Reported lesion symptoms include bothersome appearance, enlargement and burning · the affected area is the top or side of the foot · female subject, age 18–29 · close-up view · the patient considered this a rash:
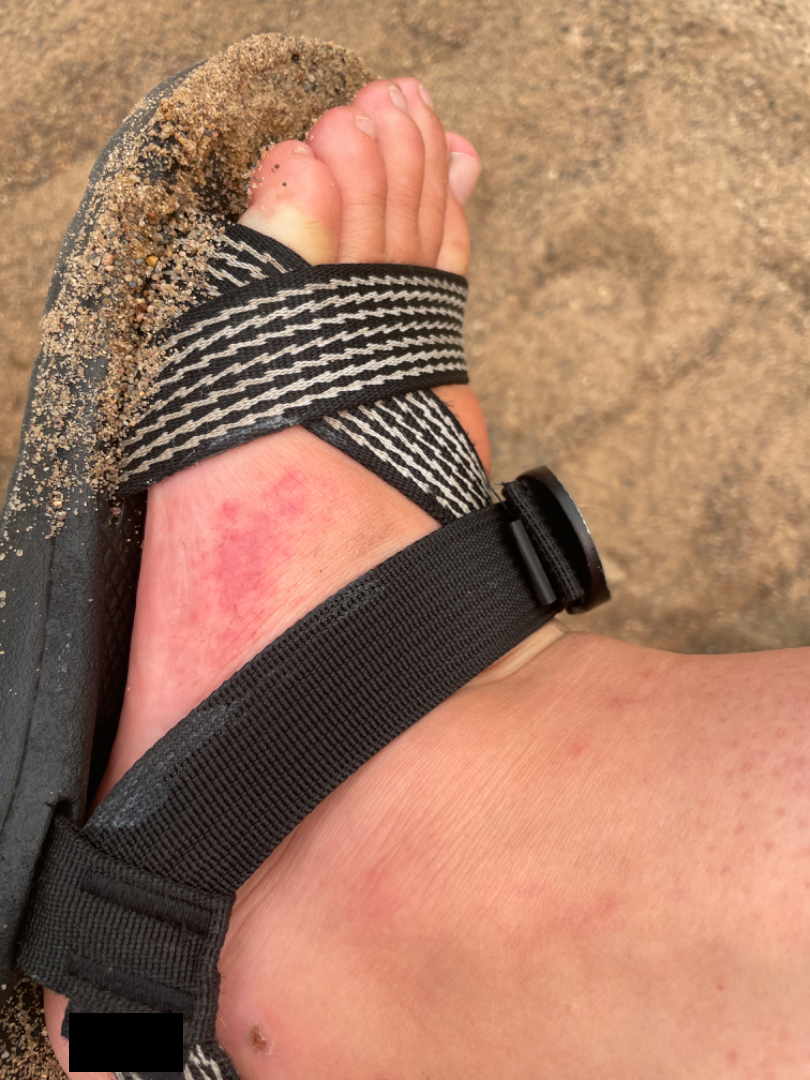<summary>
<assessment>indeterminate from the photograph</assessment>
</summary>